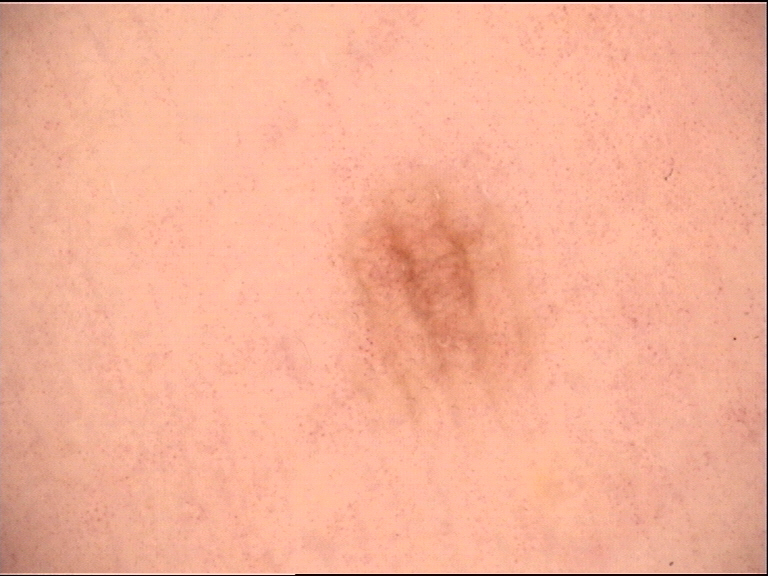A dermoscopic close-up of a skin lesion.
Consistent with a benign lesion — an acral dysplastic junctional nevus.